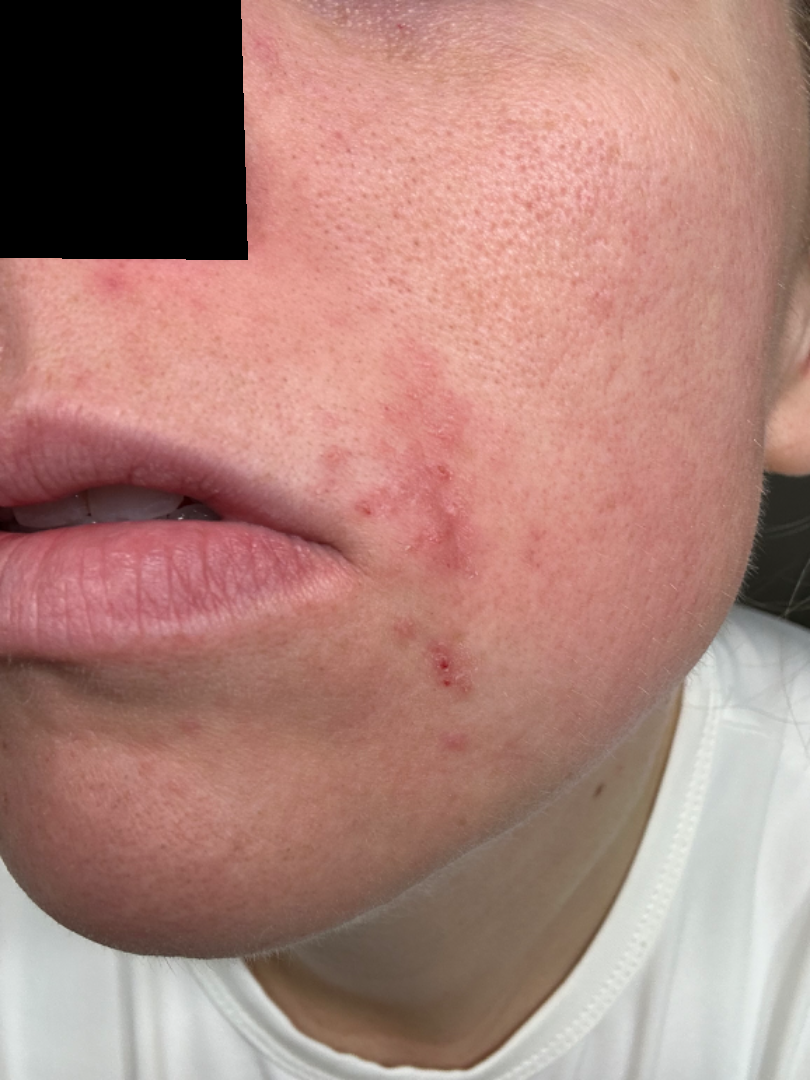<report>
<shot_type>at a distance</shot_type>
<differential>
  <leading>Perioral Dermatitis</leading>
  <considered>Impetigo, Herpes Simplex</considered>
</differential>
</report>